Present for about one day. The contributor notes the lesion is rough or flaky and raised or bumpy. Symptoms reported: itching, bothersome appearance and burning. The lesion involves the front of the torso, back of the torso and head or neck. The patient described the issue as a rash. The photograph was taken at an angle. The contributor is female: 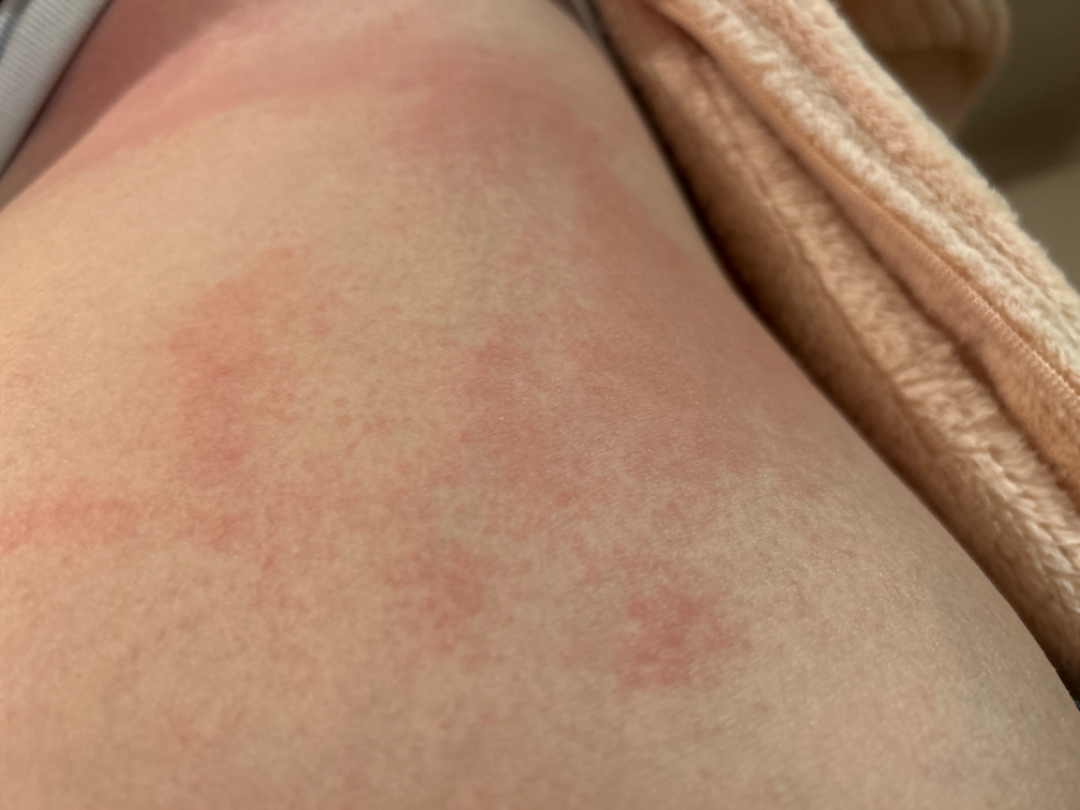Impression:
On teledermatology review: most consistent with Hypersensitivity.